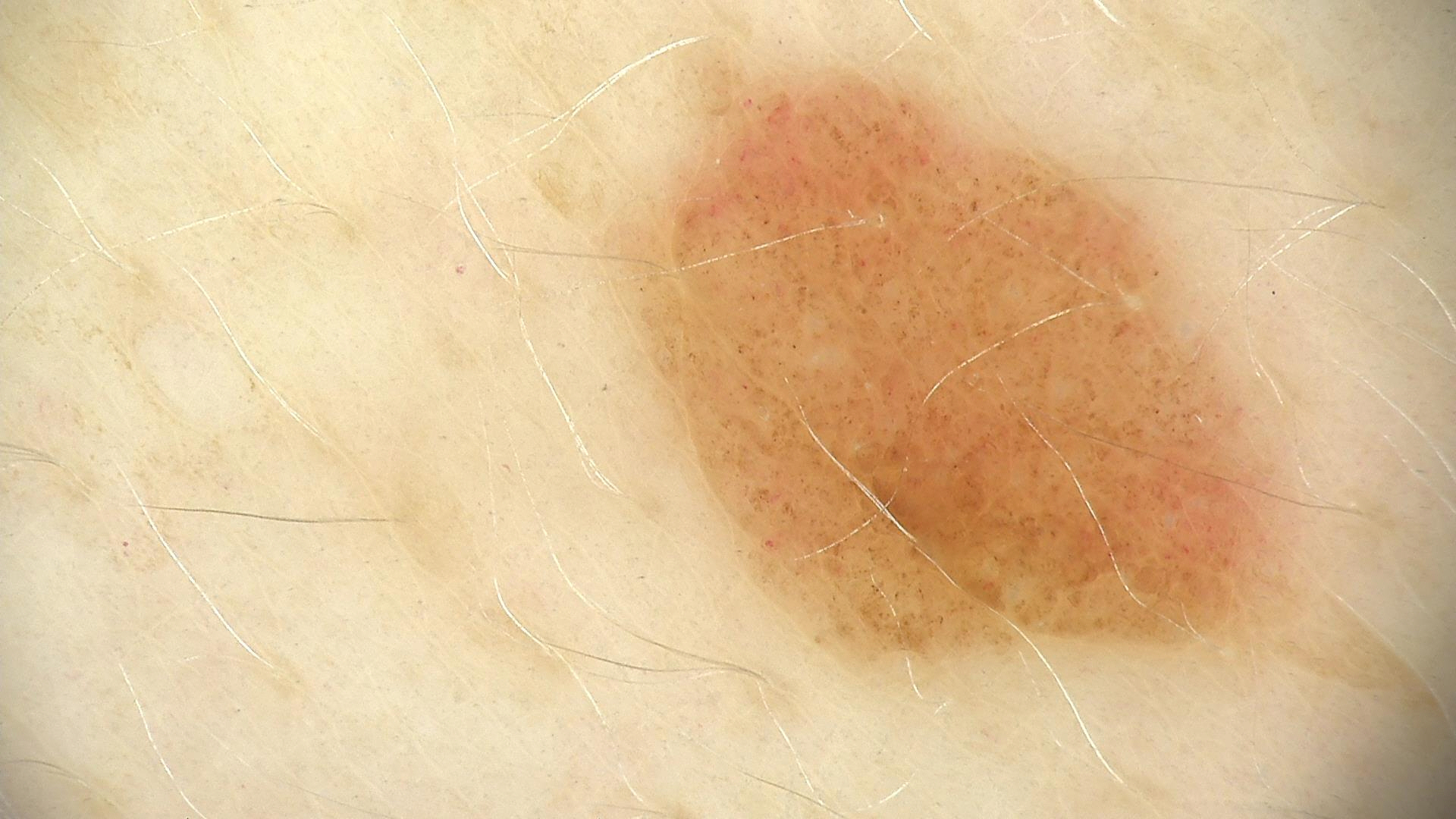Diagnosed as a compound nevus.